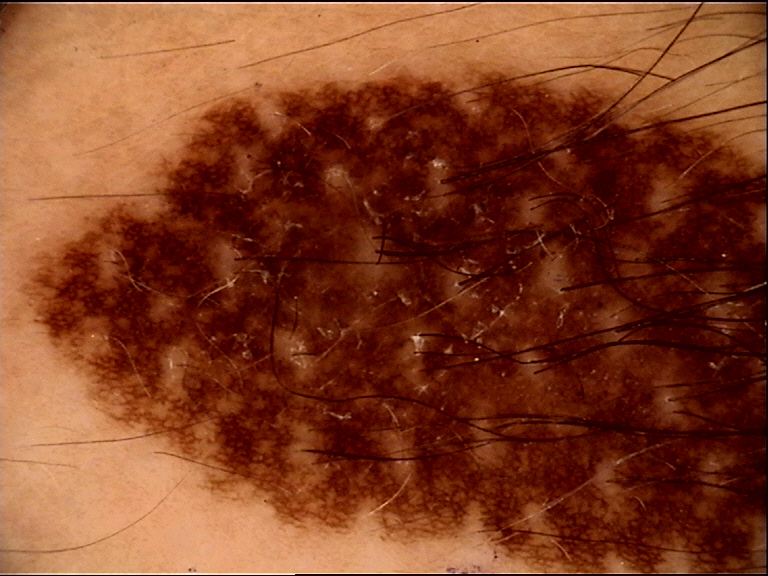A dermoscopic image of a skin lesion.
This is a banal lesion.
Labeled as a congenital compound nevus.